A contact-polarized dermoscopy image of a skin lesion; per the chart, a previous melanoma; a female patient in their mid- to late 60s; skin type I:
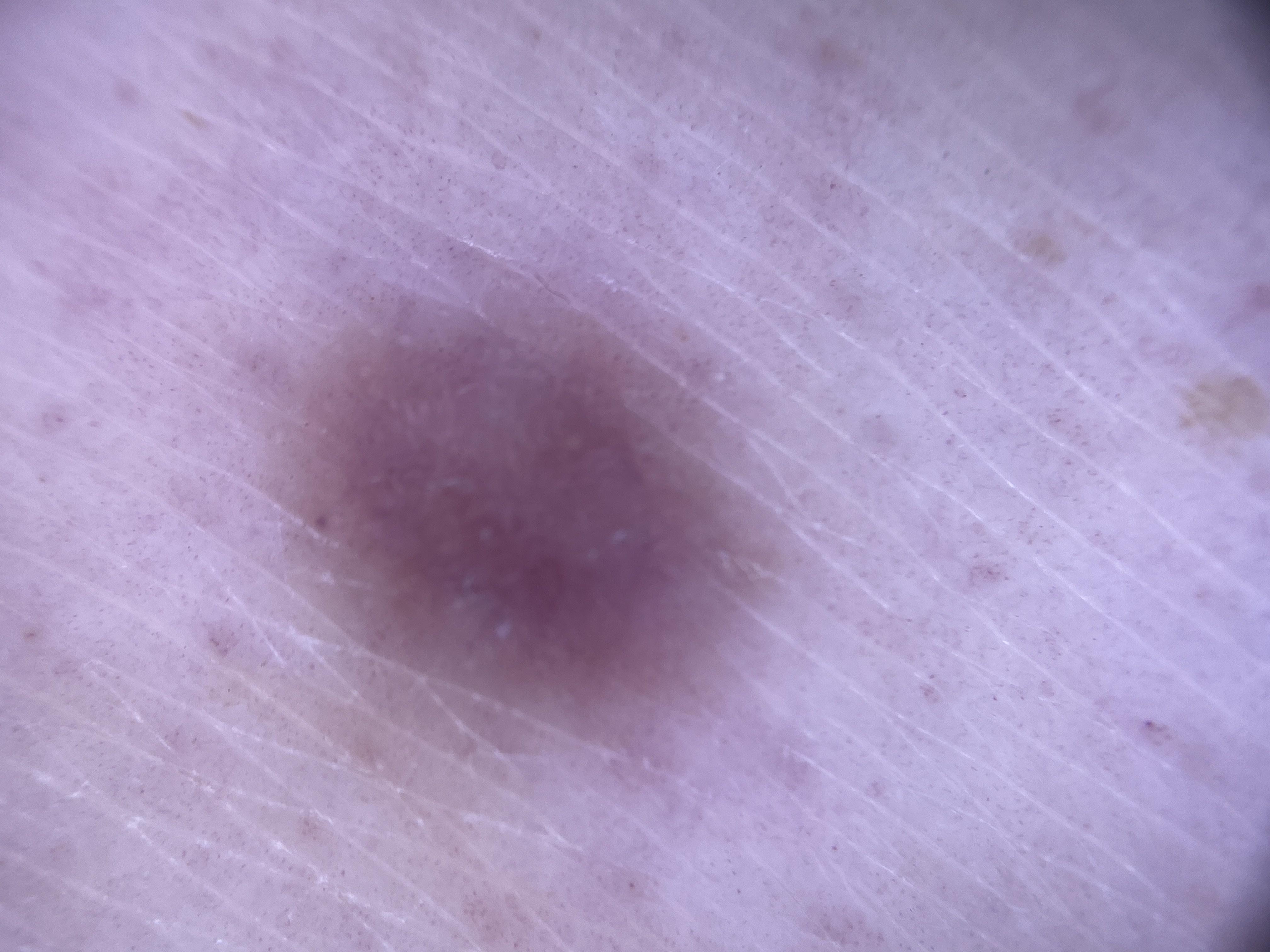site: a lower extremity | diagnostic label: Dermatofibroma (clinical impression).